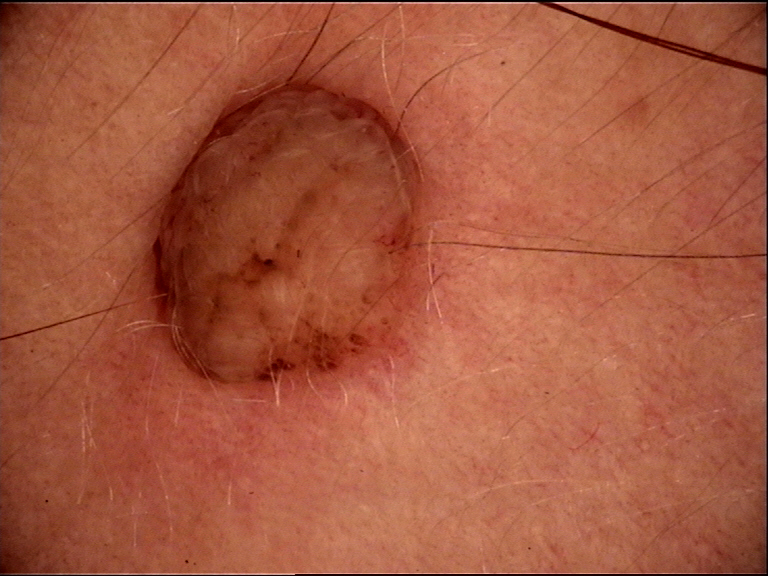Findings: Dermoscopy of a skin lesion. This is a banal lesion. Impression: The diagnosis was a dermal nevus.